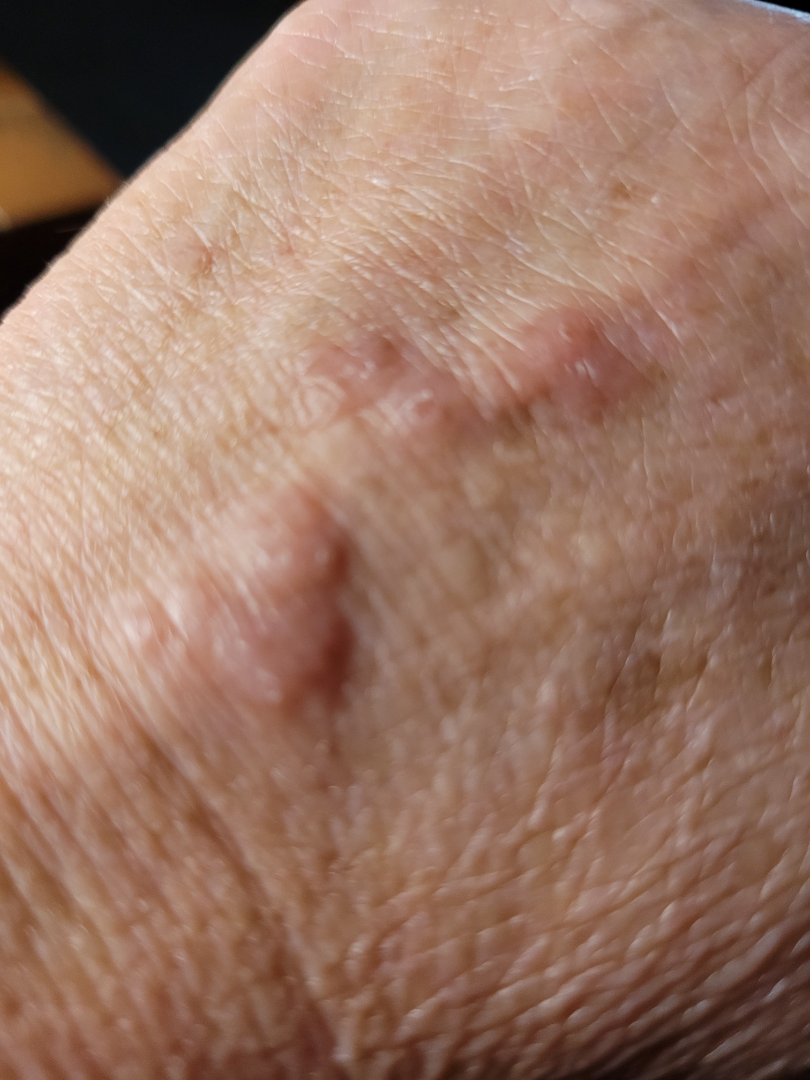No associated systemic symptoms reported. Texture is reported as rough or flaky and raised or bumpy. The contributor is female. Reported lesion symptoms include bothersome appearance. The patient notes the condition has been present for one to three months. Located on the back of the hand. Close-up view. Reviewed remotely by one dermatologist: the impression was split between Granuloma annulare and Allergic Contact Dermatitis; a remote consideration is Psoriasis.